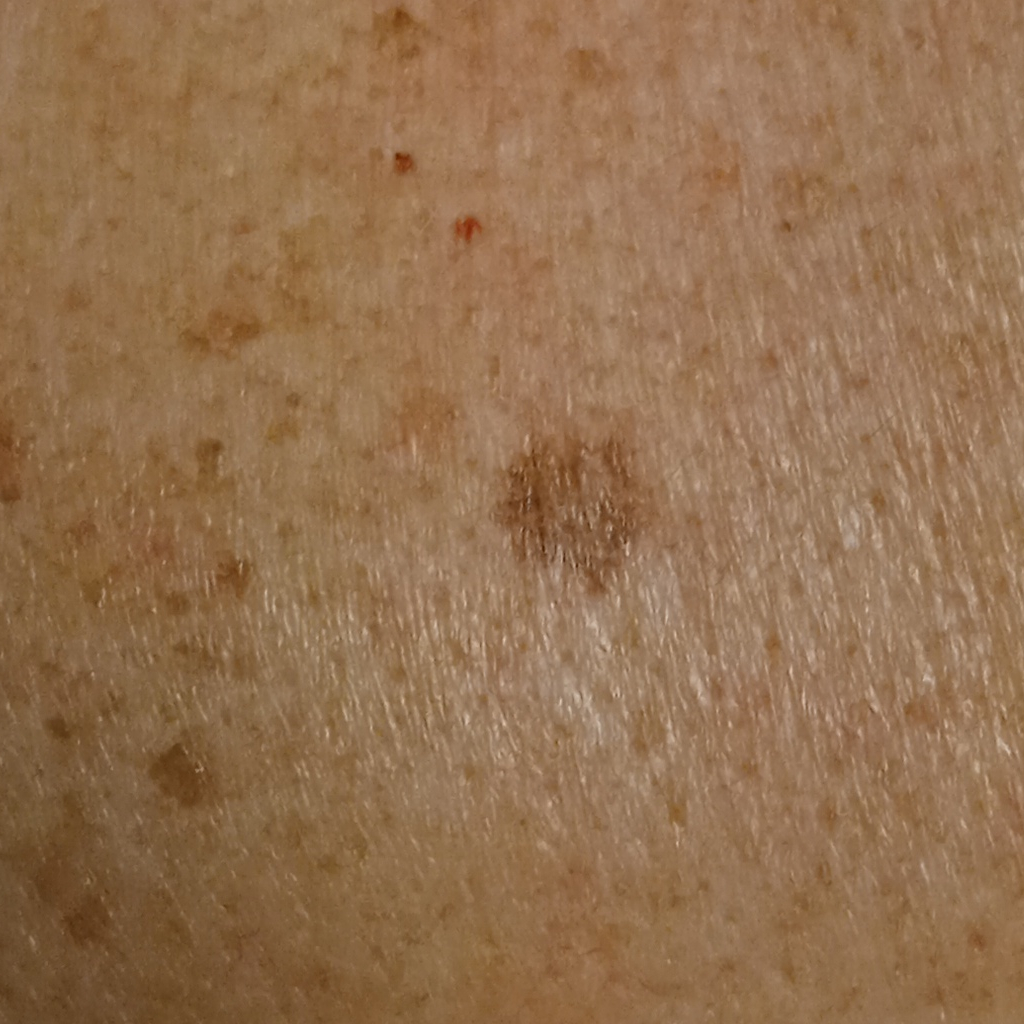The reviewing dermatologists could not reach a confident diagnosis. Q: How does the patient's skin react to sun?
A: skin reddens with sun exposure
Q: What kind of image is this?
A: clinical photo
Q: What is the patient's nevus burden?
A: few melanocytic nevi overall
Q: What is the referral context?
A: research study (no referral diagnosis)
Q: Patient demographics?
A: male, aged 81
Q: Where is the lesion?
A: the back
Q: How large is the lesion?
A: 8 mm